The photo was captured at an angle: 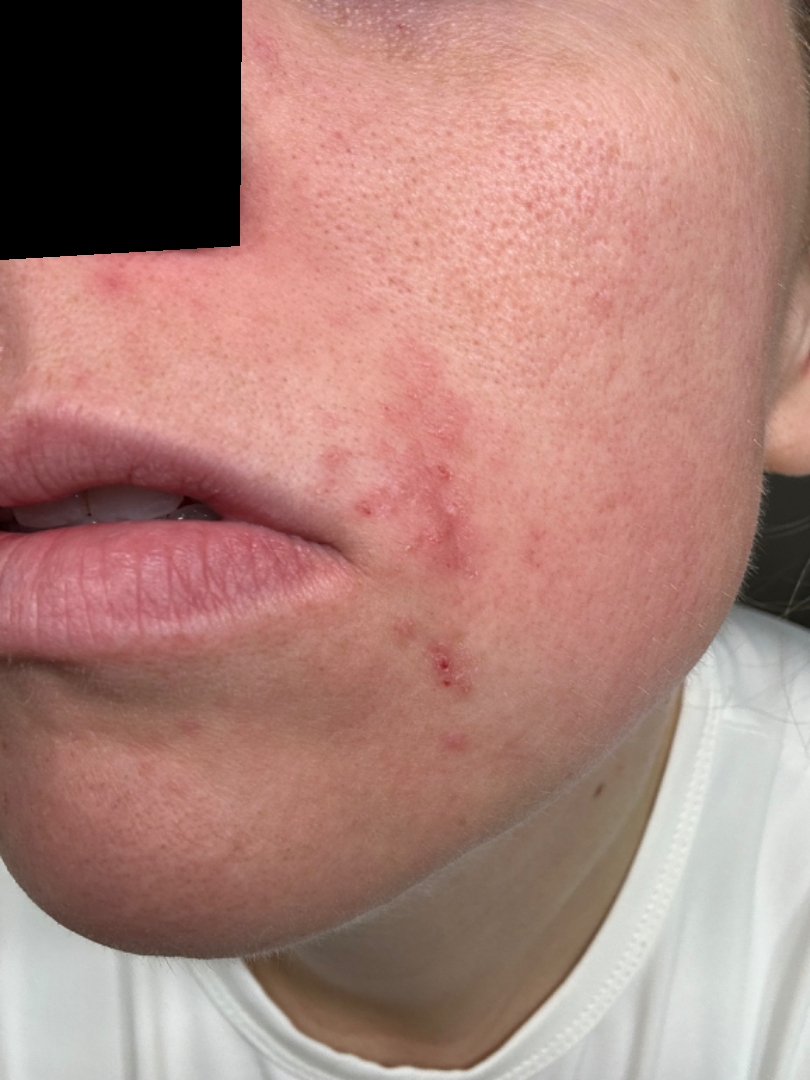differential:
  leading:
    - Perioral Dermatitis
  considered:
    - Impetigo
    - Herpes Simplex